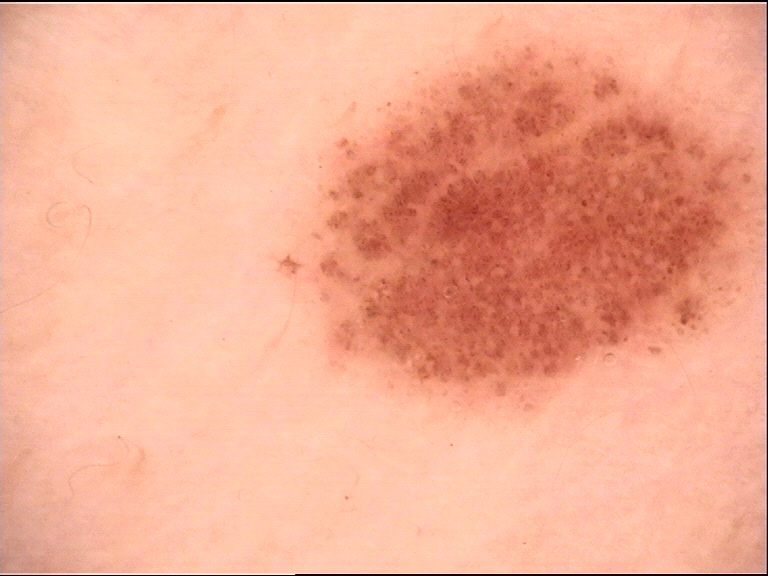Case: A dermatoscopic image of a skin lesion. Impression: Classified as a dysplastic junctional nevus.